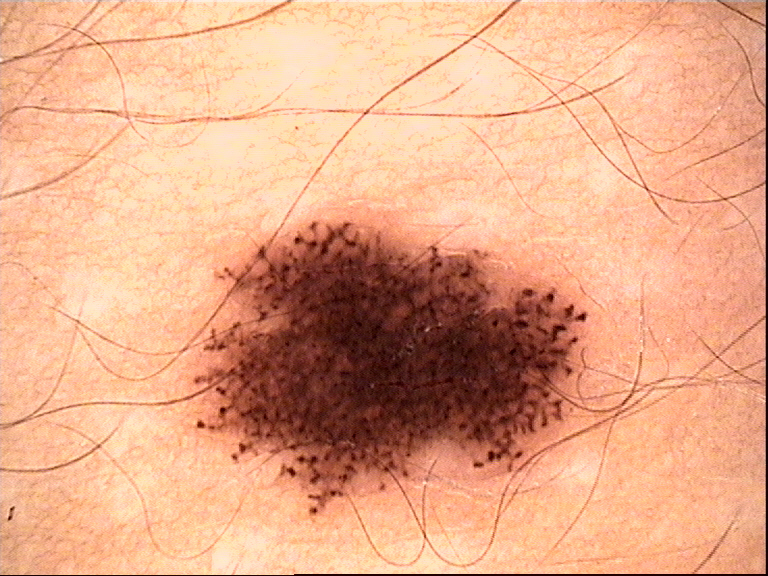Conclusion:
The diagnosis was a dysplastic junctional nevus.